A male patient about 45 years old · a wide-field clinical photograph of a skin lesion · Fitzpatrick I:
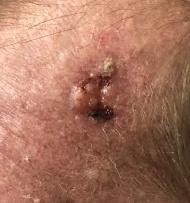site=the head or neck | pathology=Basal cell carcinoma (biopsy-proven).